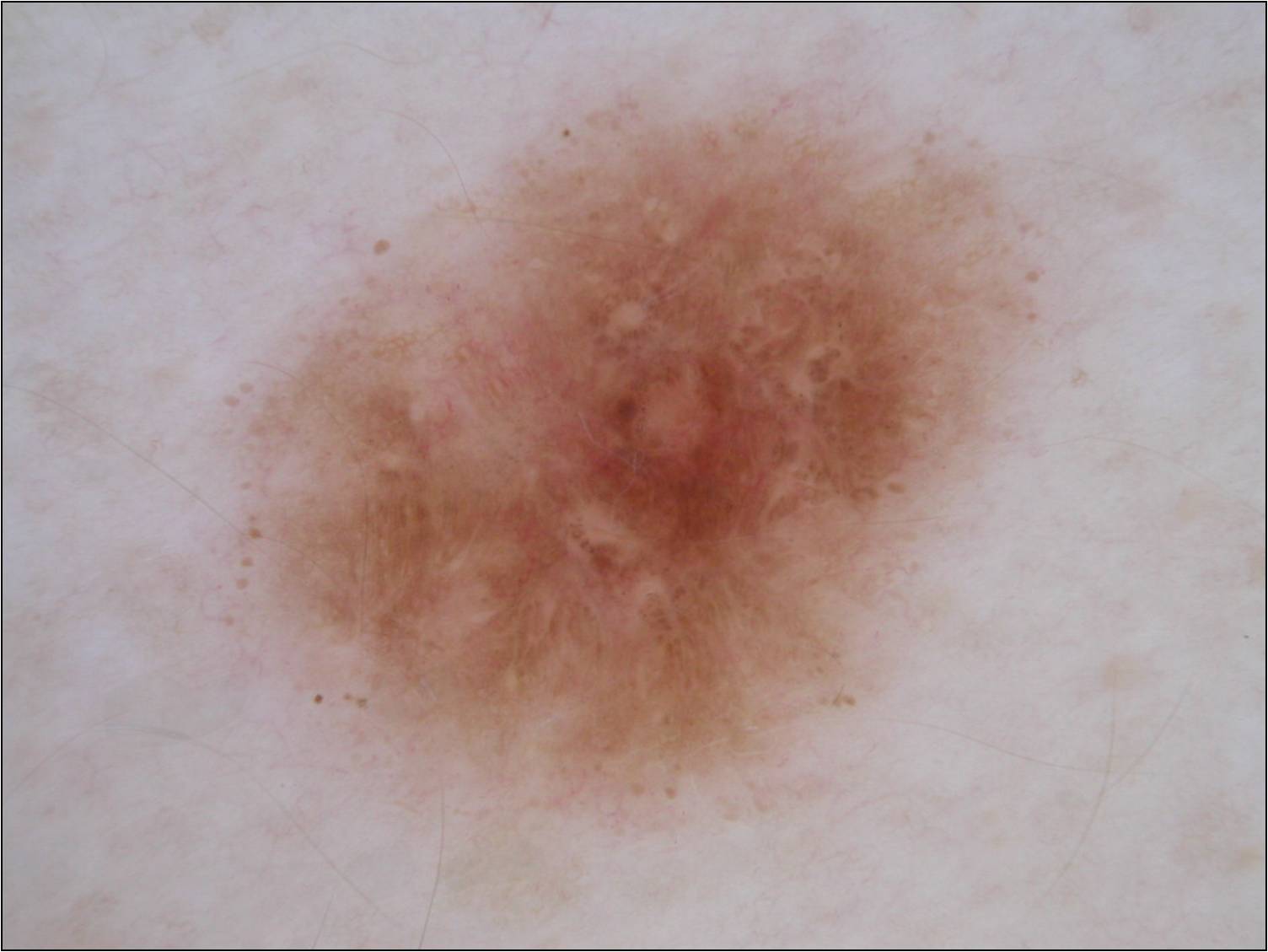A dermatoscopic image of a skin lesion.
A large lesion occupying much of the field.
The lesion is bounded by x1=195 y1=66 x2=1114 y2=923.
Dermoscopic assessment notes globules; no streaks.
The clinical diagnosis was a benign skin lesion.